A dermoscopy image of a single skin lesion, the subject is a female in their mid-30s — 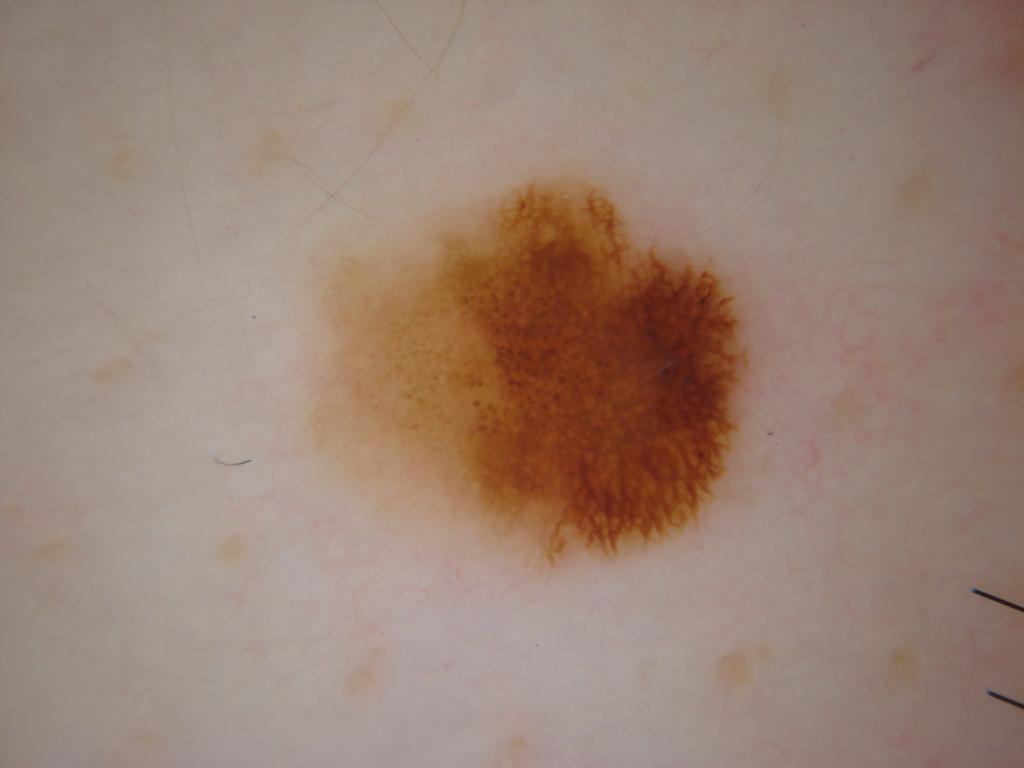Case summary:
Dermoscopy demonstrates globules and pigment network. The lesion takes up about 17% of the image. The lesion is located at <box>306, 174, 754, 581</box>.
Impression:
Clinically diagnosed as a melanocytic nevus, a benign skin lesion.